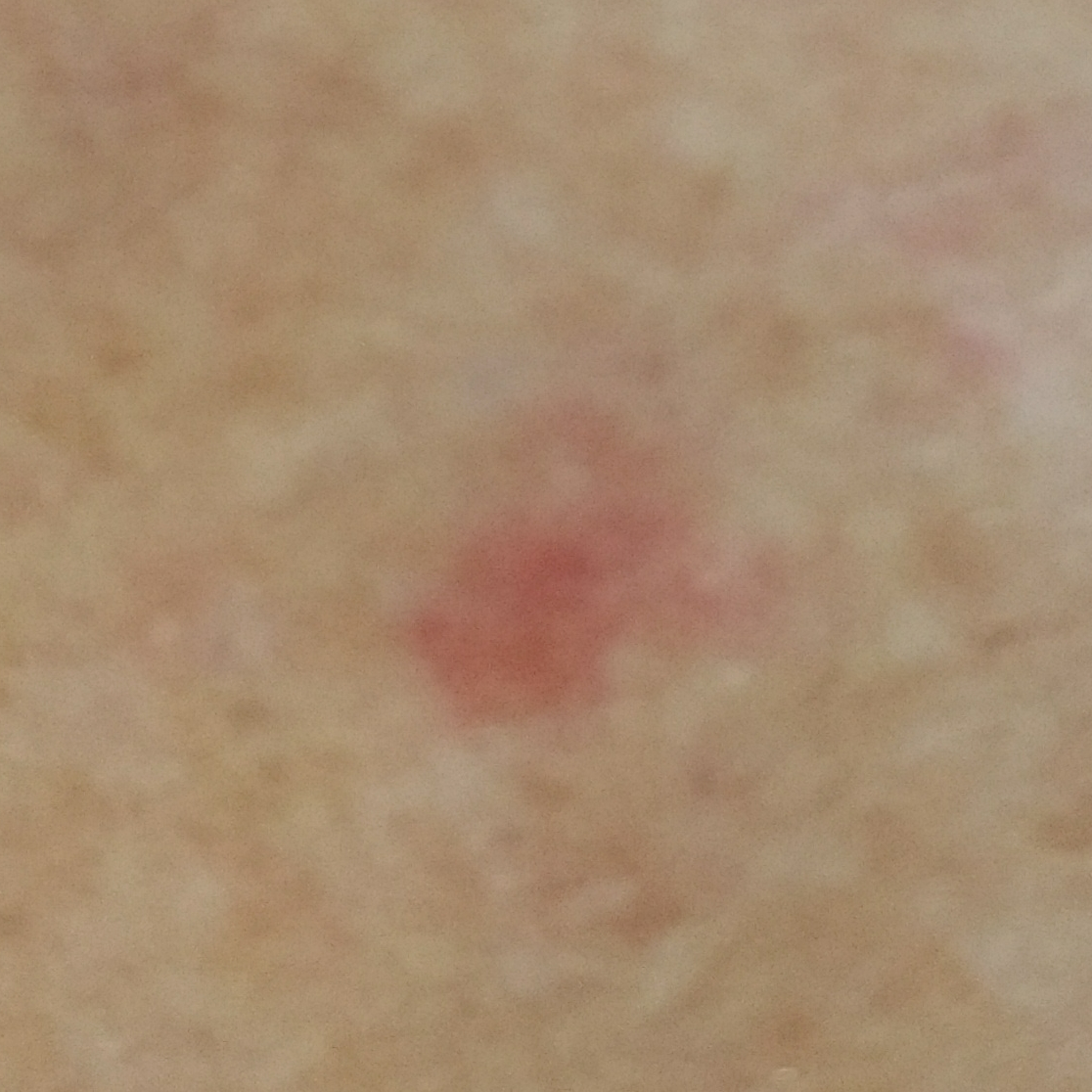<case>
<patient>
<age>61</age>
<gender>female</gender>
</patient>
<image>clinical photo</image>
<skin_type>II</skin_type>
<lesion_location>an arm</lesion_location>
<lesion_size>
<diameter_1_mm>10.0</diameter_1_mm>
<diameter_2_mm>10.0</diameter_2_mm>
</lesion_size>
<diagnosis>
<name>actinic keratosis</name>
<code>ACK</code>
<malignancy>indeterminate</malignancy>
<confirmation>histopathology</confirmation>
</diagnosis>
</case>